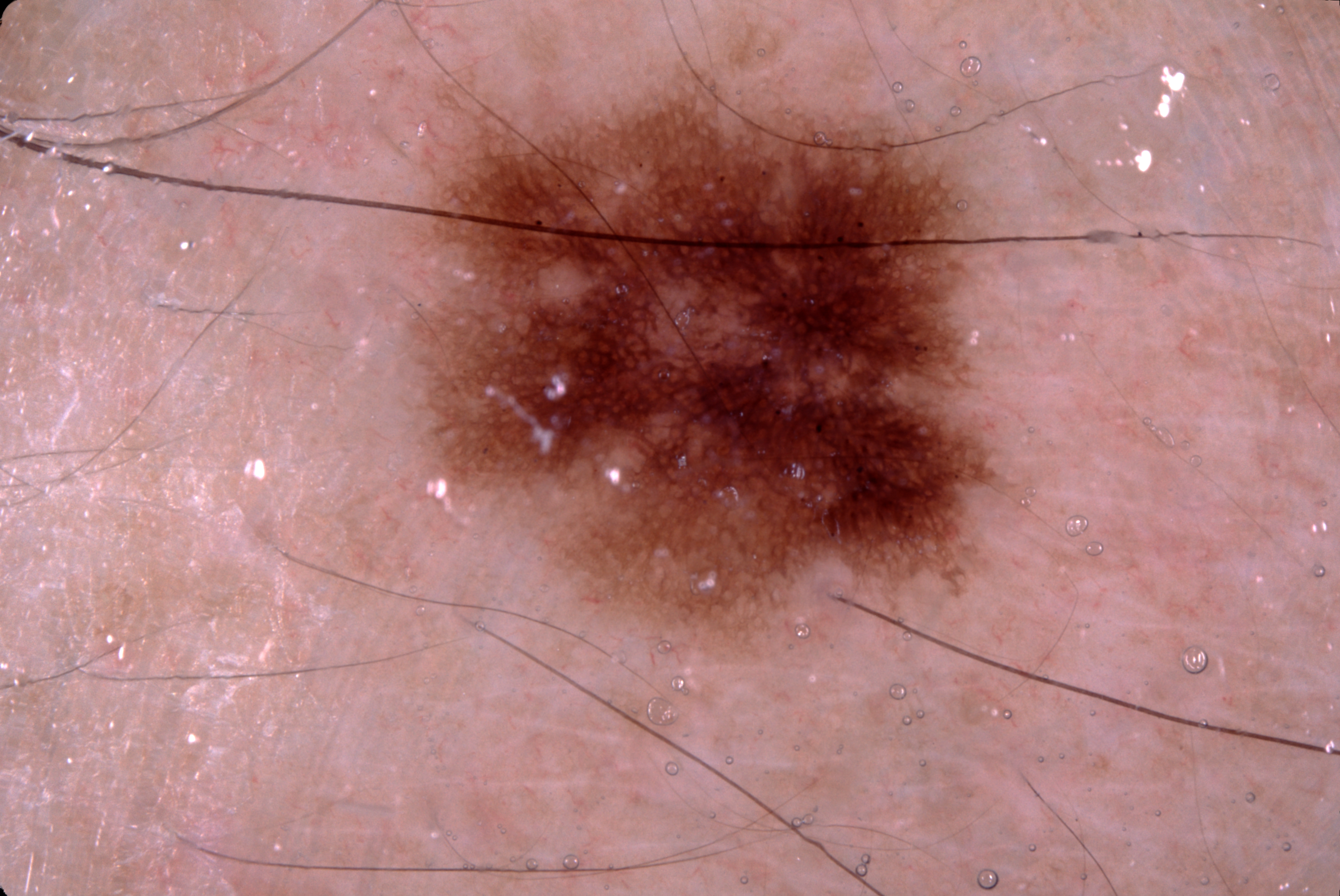A dermoscopy image of a single skin lesion. The subject is a male approximately 50 years of age. The lesion covers approximately 28% of the dermoscopic field. The lesion occupies the region left=390, top=33, right=1044, bottom=683. Dermoscopic review identifies pigment network; no negative network, milia-like cysts, or streaks. The lesion was assessed as a melanocytic nevus.